Dermoscopy of a skin lesion:
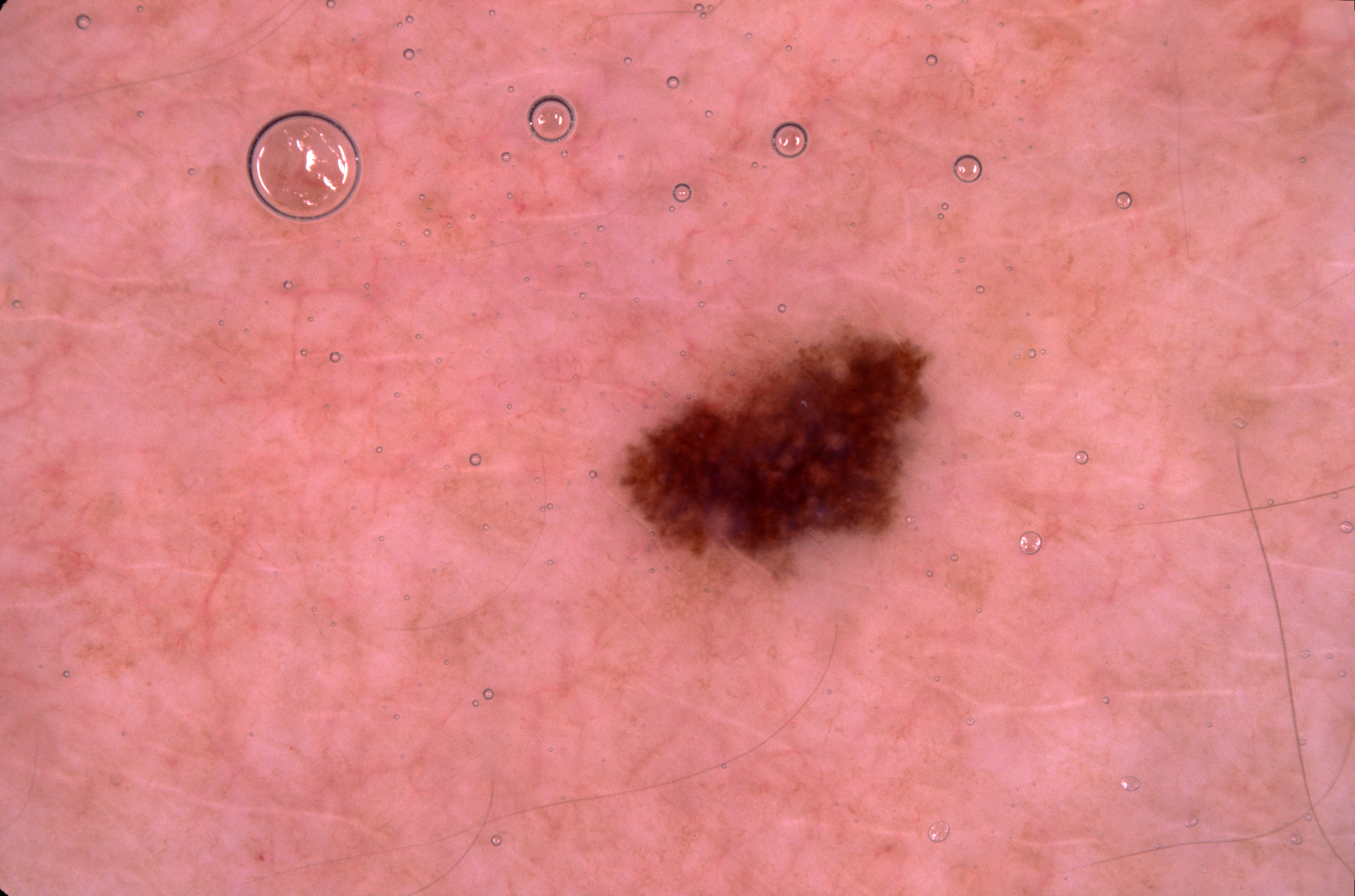<record>
  <lesion_extent>
    <approx_field_fraction_pct>5</approx_field_fraction_pct>
  </lesion_extent>
  <lesion_location>
    <bbox_xyxy>612, 318, 935, 600</bbox_xyxy>
  </lesion_location>
  <dermoscopic_features>
    <present/>
    <absent>streaks, negative network, milia-like cysts, pigment network</absent>
  </dermoscopic_features>
  <diagnosis>
    <name>melanocytic nevus</name>
    <malignancy>benign</malignancy>
    <lineage>melanocytic</lineage>
    <provenance>clinical</provenance>
  </diagnosis>
</record>